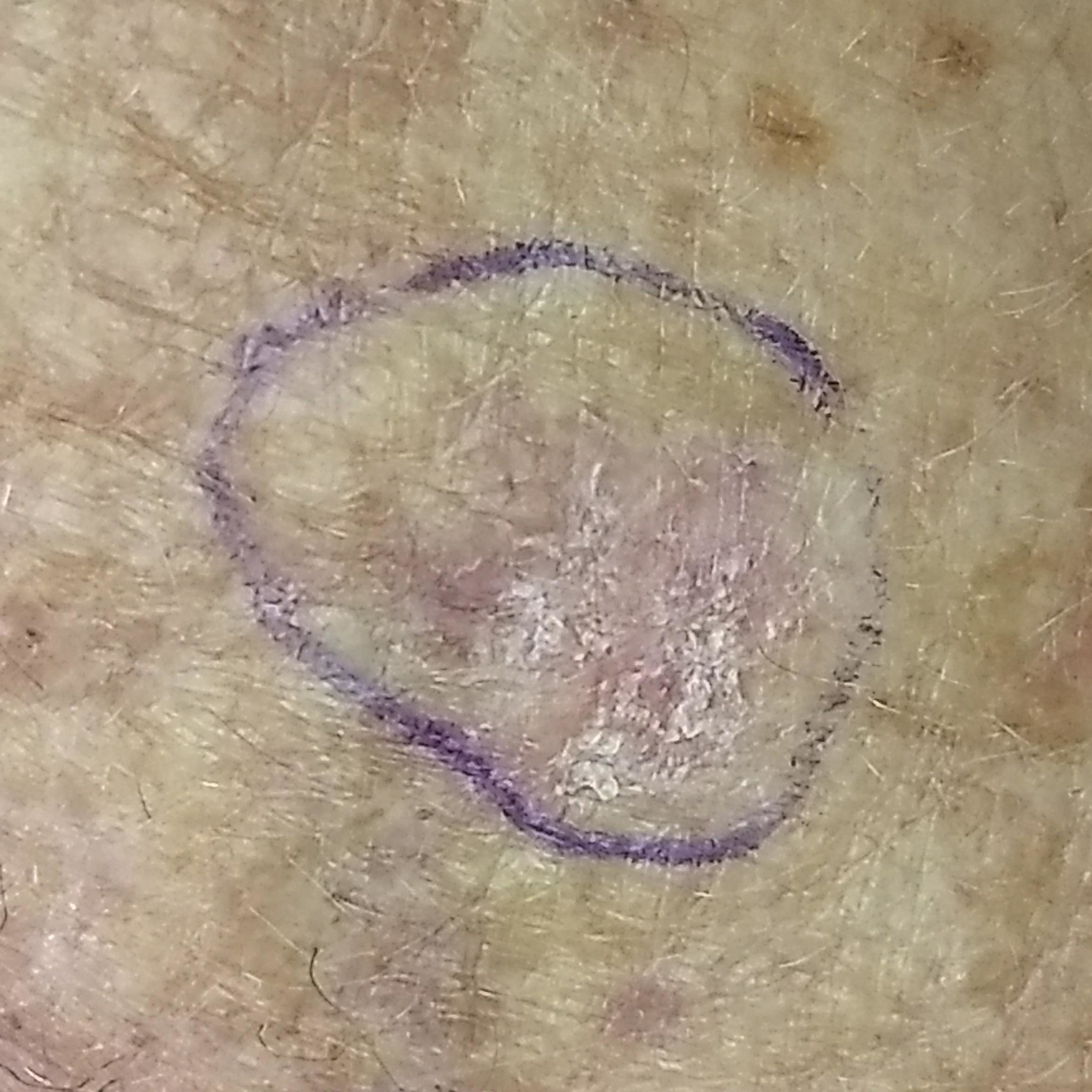Q: Who is the patient?
A: 65 years of age
Q: What was the clinical impression?
A: actinic keratosis (clinical consensus)